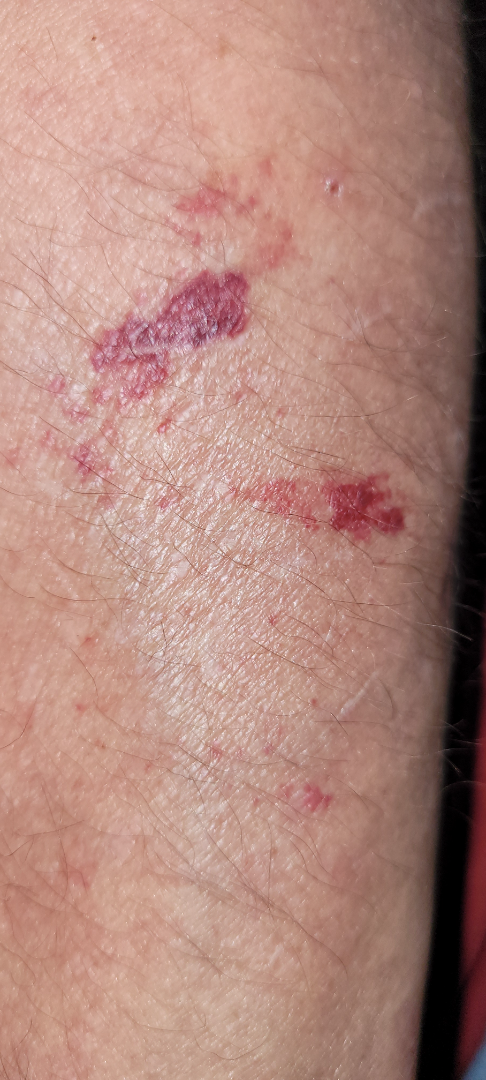Q: What conditions are considered?
A: in keeping with ecchymoses